The photograph is a close-up of the affected area: 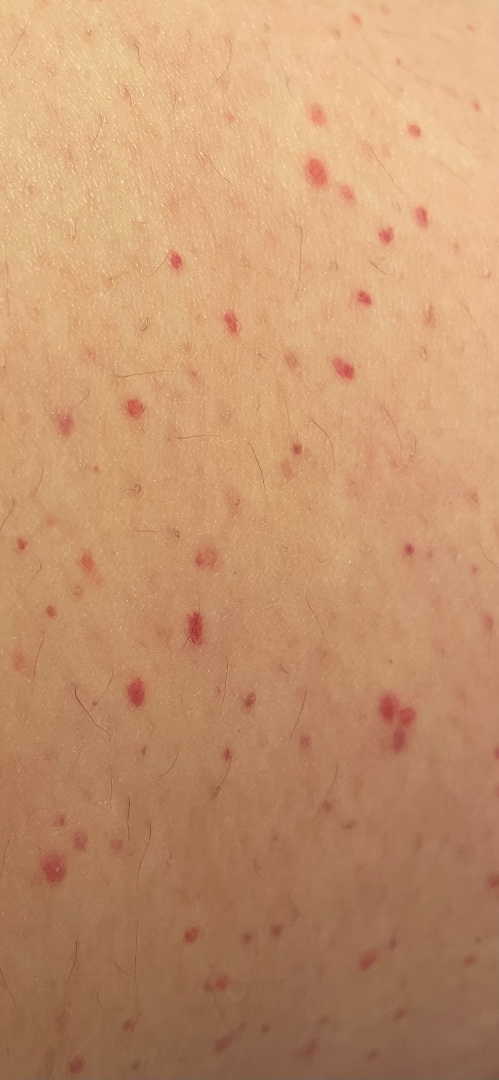• skin tone: Fitzpatrick phototype II
• clinical impression: the differential, in no particular order, includes Purpura and Vasculitis of the skin